The photograph is a close-up of the affected area — 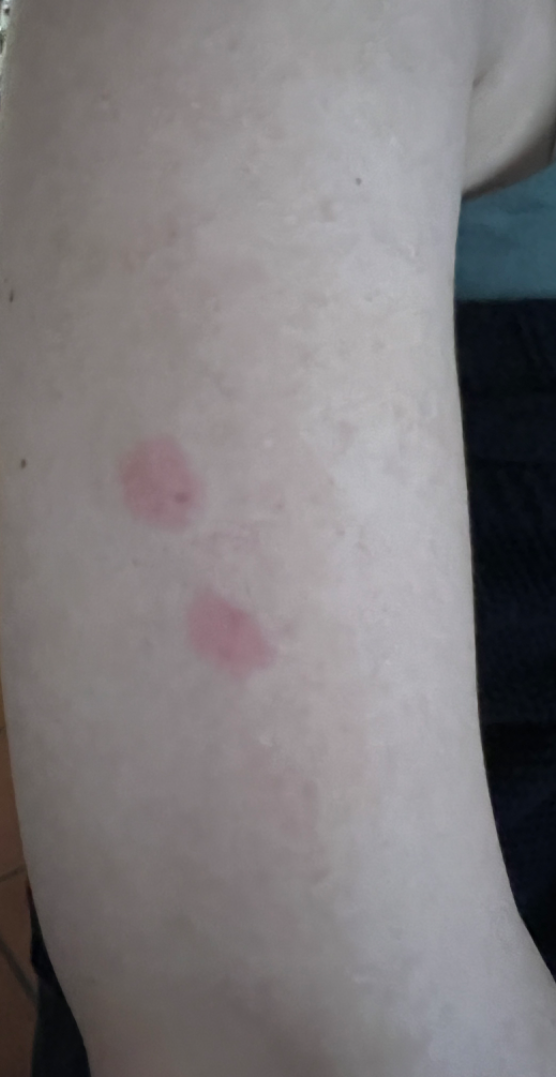Case summary:
* diagnostic considerations · the differential, in no particular order, includes Urticaria, Insect Bite and Allergic Contact Dermatitis